The patient reports a personal history of cancer, a personal history of skin cancer, and no prior organ transplant · collected as part of a research study, without a referral diagnosis · the patient says their skin tans without first burning · a moderate number of moles by the patient's own estimate · a female subject 75 years of age · a clinical close-up of a skin lesion — 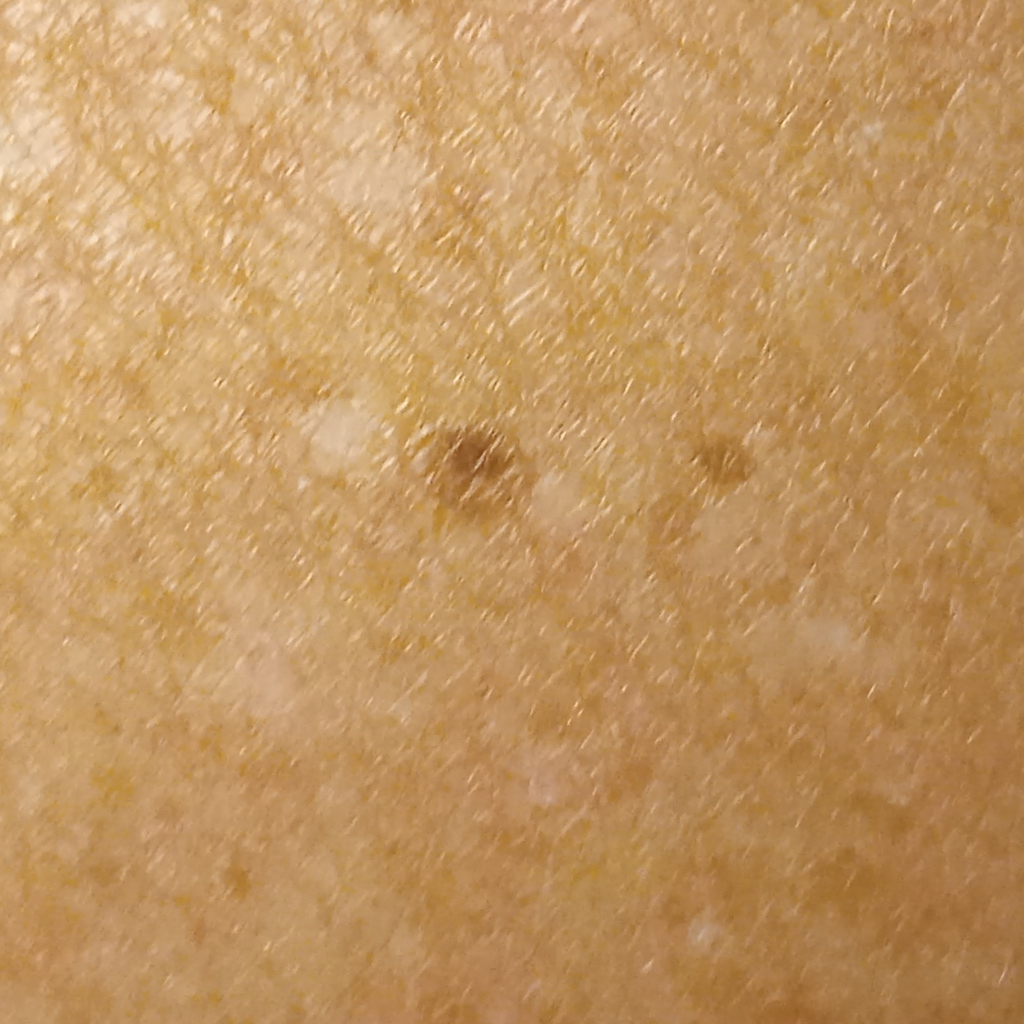Findings:
Located on the back. The lesion is about 2.7 mm across.
Impression:
Dermatologist review favored a melanocytic nevus.